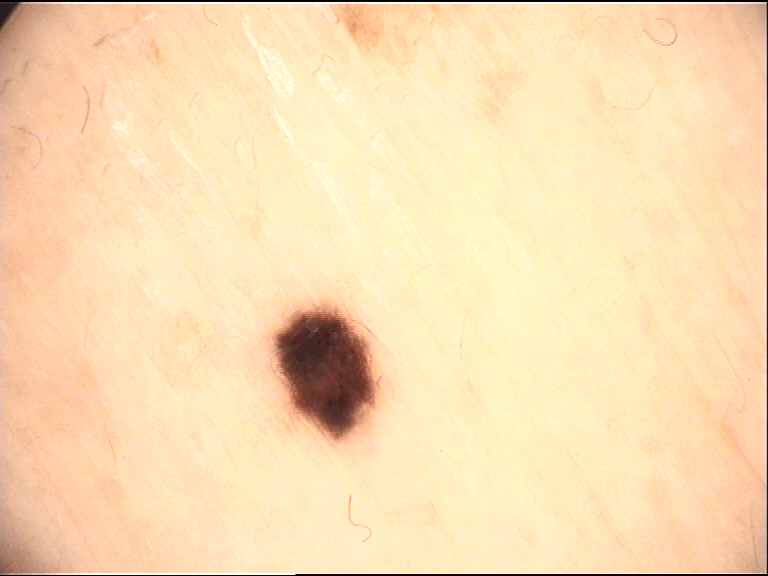The diagnostic label was a junctional nevus.